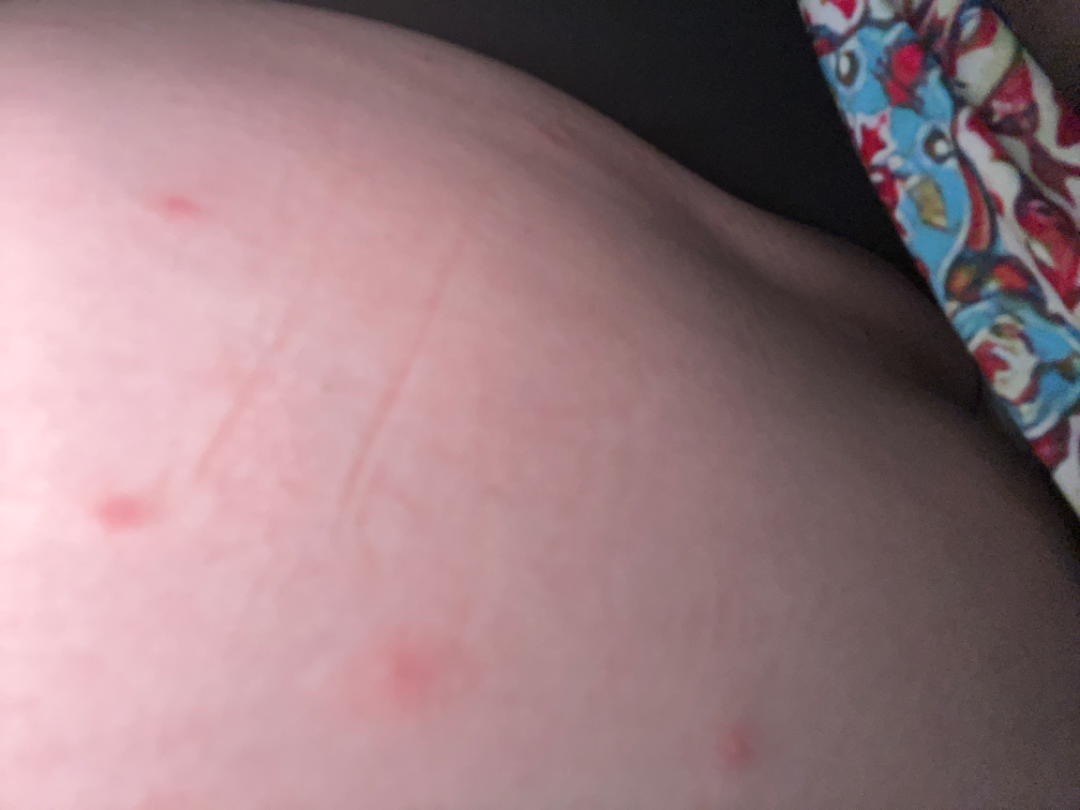* assessment: indeterminate
* patient: female, age 50–59
* location: head or neck, front of the torso and arm
* view: close-up